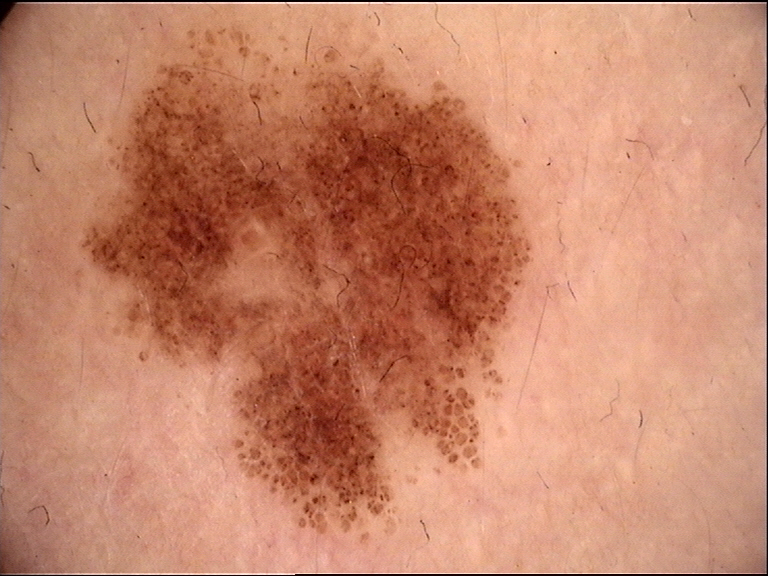A dermoscopic close-up of a skin lesion.
Diagnosed as a benign lesion — a dysplastic junctional nevus.